Imaged for a research study, with no referral diagnosis recorded · a female patient 59 years old:
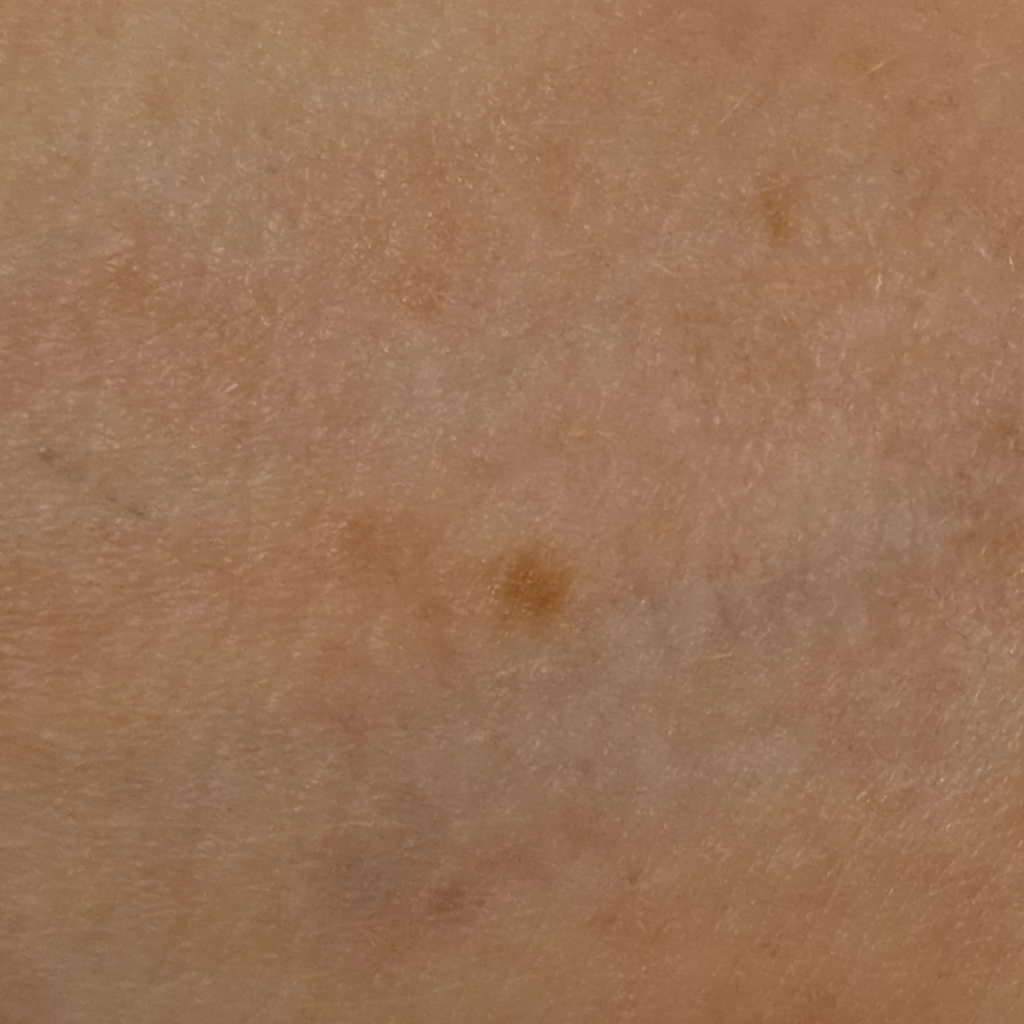Measuring roughly 6.5 mm. Dermatologist review favored a melanocytic nevus.